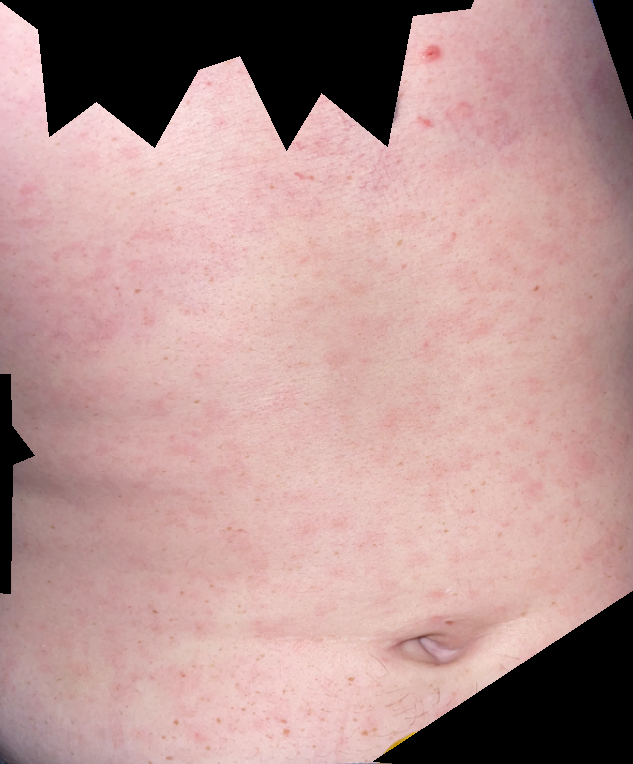framing: close-up, dermatologist impression: the differential is split between Drug Rash and Viral Exanthem; less probable is Folliculitis.